The photograph was taken at an angle. The patient indicates the condition has been present for more than one year. The patient reported no systemic symptoms. Located on the top or side of the foot, head or neck, leg, front of the torso, back of the torso, back of the hand and arm. The lesion is described as raised or bumpy and rough or flaky. Reported lesion symptoms include bothersome appearance and itching. Self-categorized by the patient as a rash:
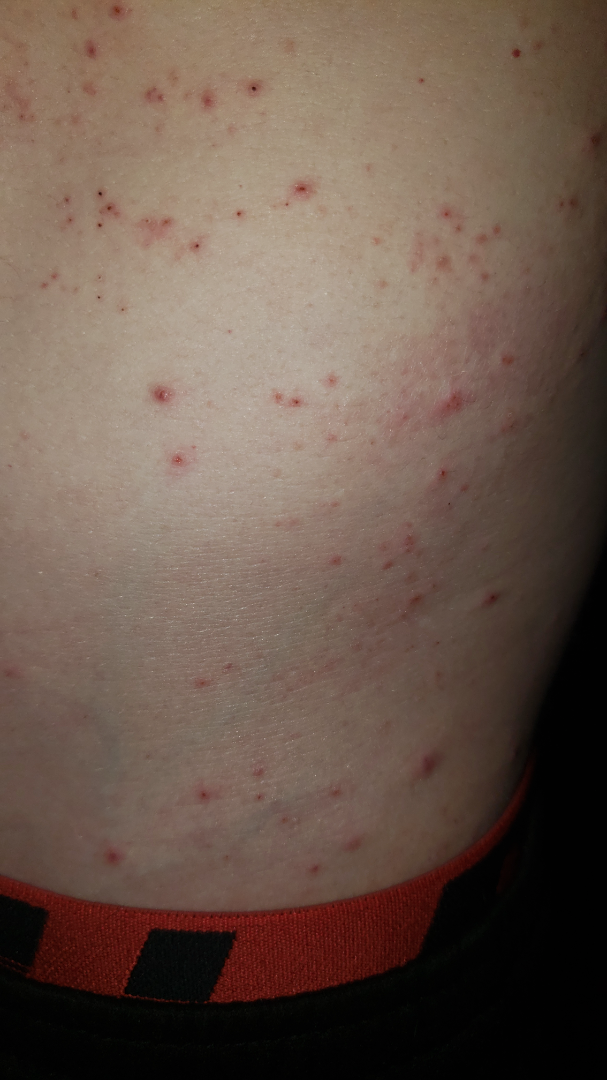assessment = indeterminate from the photograph.